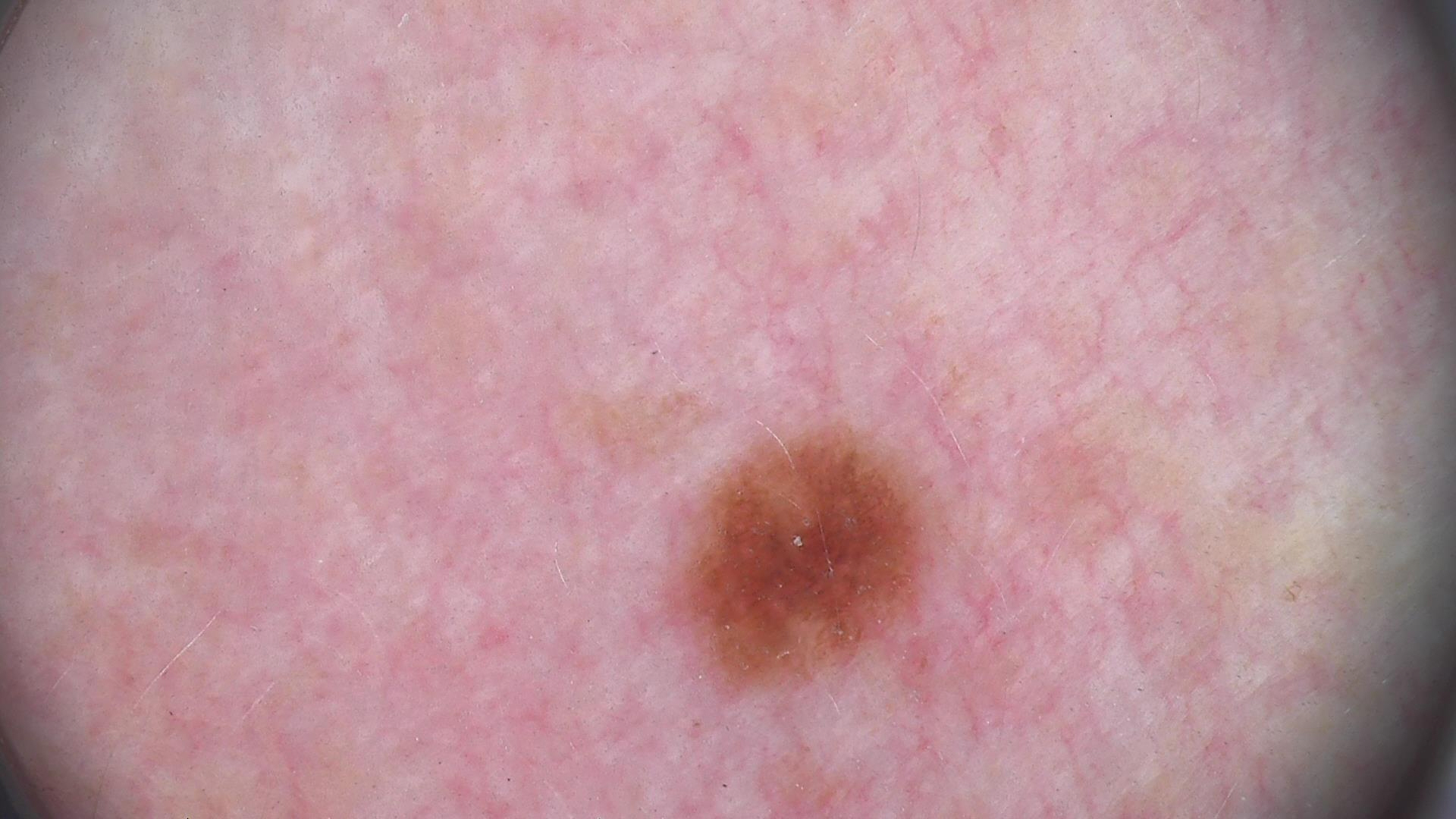modality: dermoscopy | diagnosis: dysplastic junctional nevus (expert consensus).